A dermoscopic view of a skin lesion.
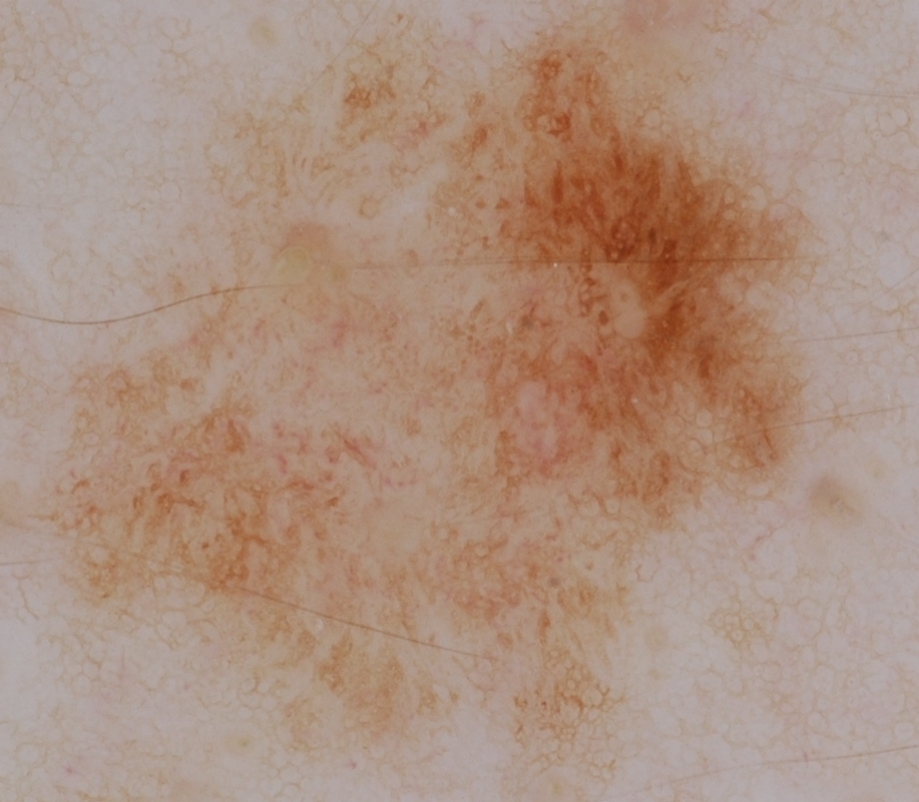With coordinates (x1, y1, x2, y2), the lesion is bounded by bbox(47, 0, 818, 741). Dermoscopic review identifies globules; no pigment network, streaks, negative network, or milia-like cysts. Consistent with a melanocytic nevus.